A dermoscopy image of a single skin lesion. The patient is a female aged around 40.
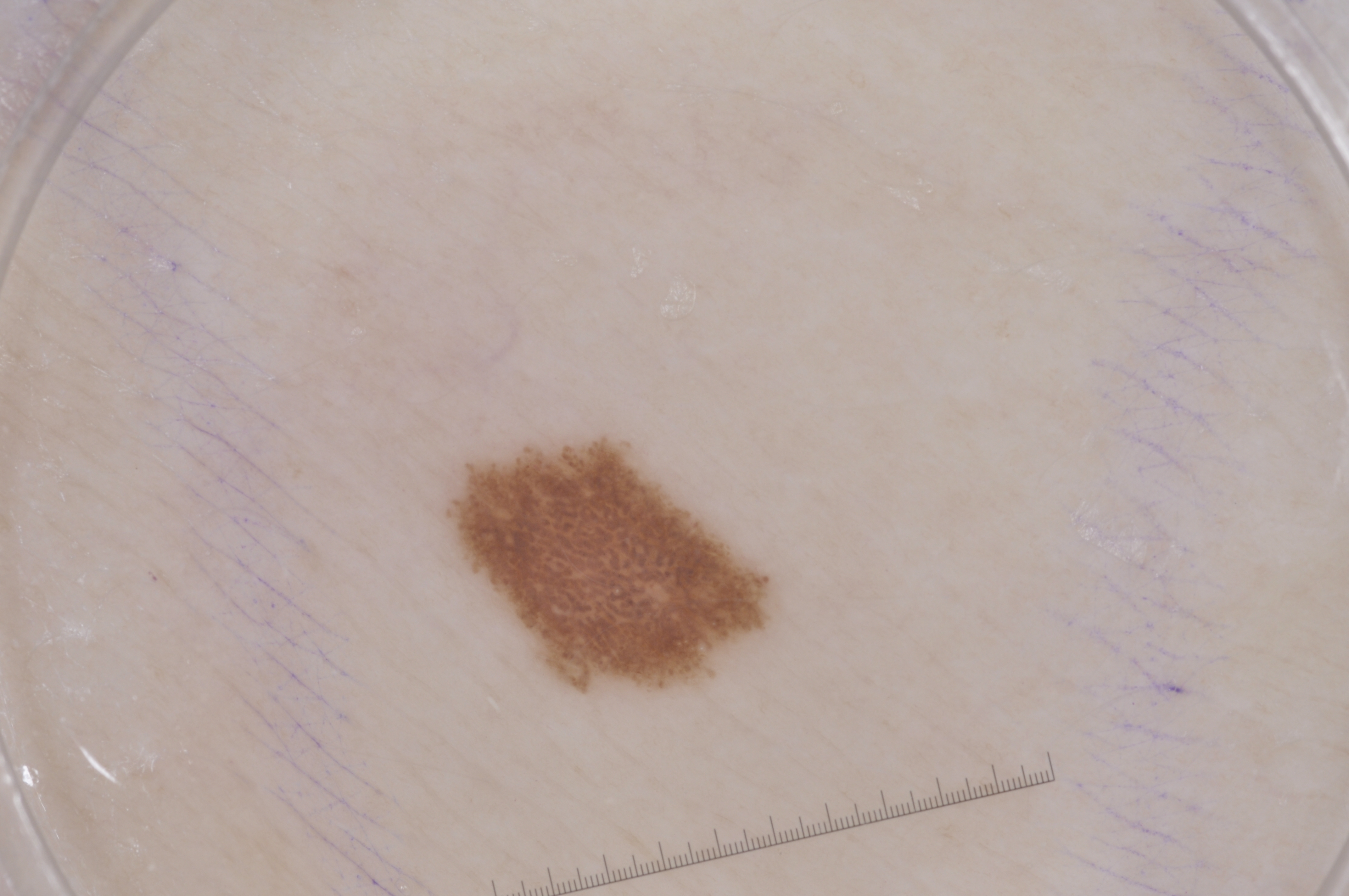{"dermoscopic_features": {"present": ["negative network", "milia-like cysts"], "absent": ["pigment network", "streaks"]}, "lesion_location": {"bbox_xyxy": [442, 434, 779, 695]}, "diagnosis": {"name": "melanocytic nevus", "malignancy": "benign", "lineage": "melanocytic", "provenance": "clinical"}}